The photo was captured at an angle · located on the front of the torso, leg and back of the torso: 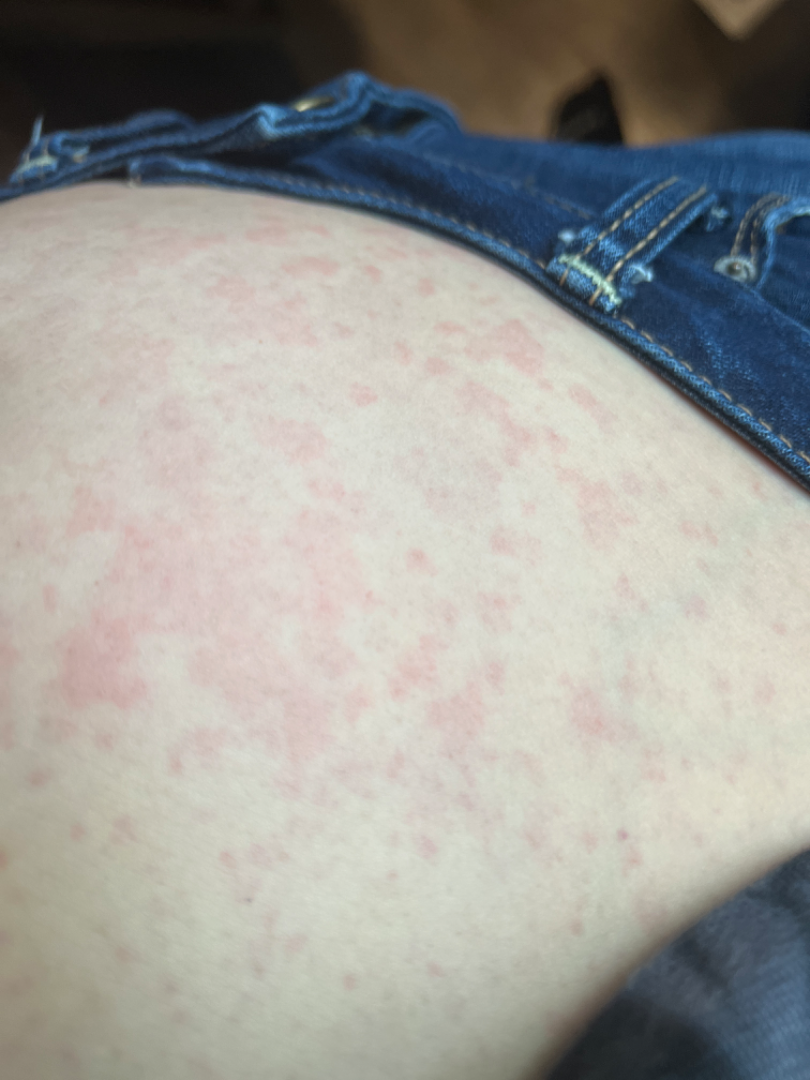Associated systemic symptoms include fatigue. The contributor reports itching, pain and bothersome appearance. Texture is reported as raised or bumpy. Present for less than one week. The reviewing clinician's impression was: Hypersensitivity and Allergic Contact Dermatitis were considered with similar weight; a remote consideration is Viral Exanthem.